A dermatoscopic image of a skin lesion: 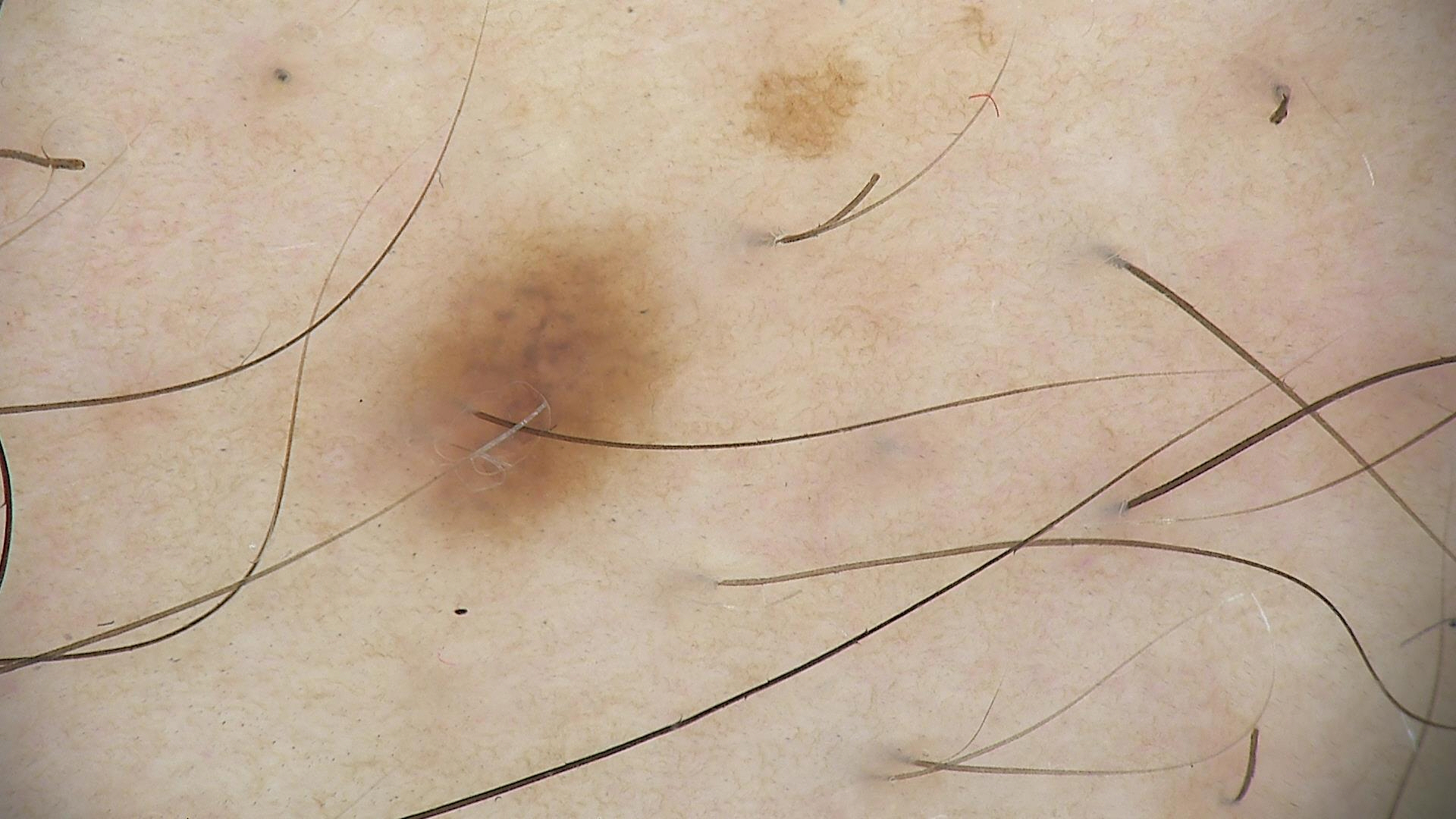diagnostic label: dysplastic junctional nevus (expert consensus).